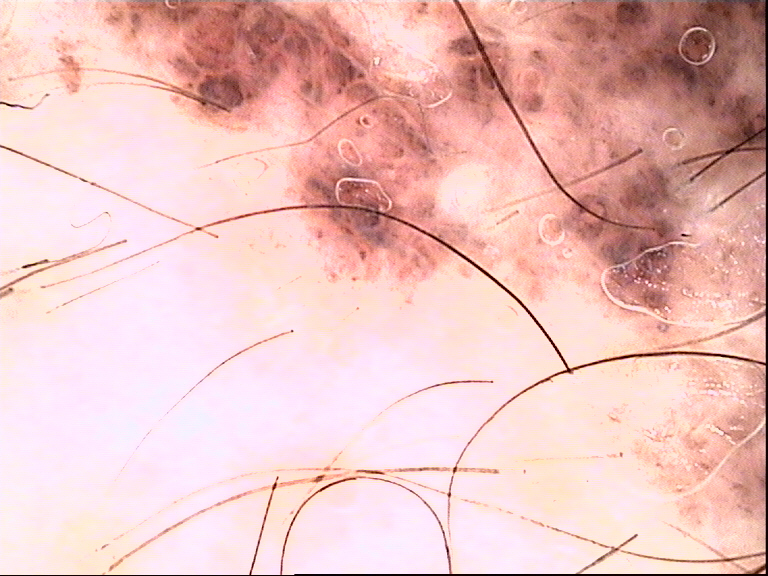A dermatoscopic image of a skin lesion. This is a banal lesion. Labeled as a congenital compound nevus.